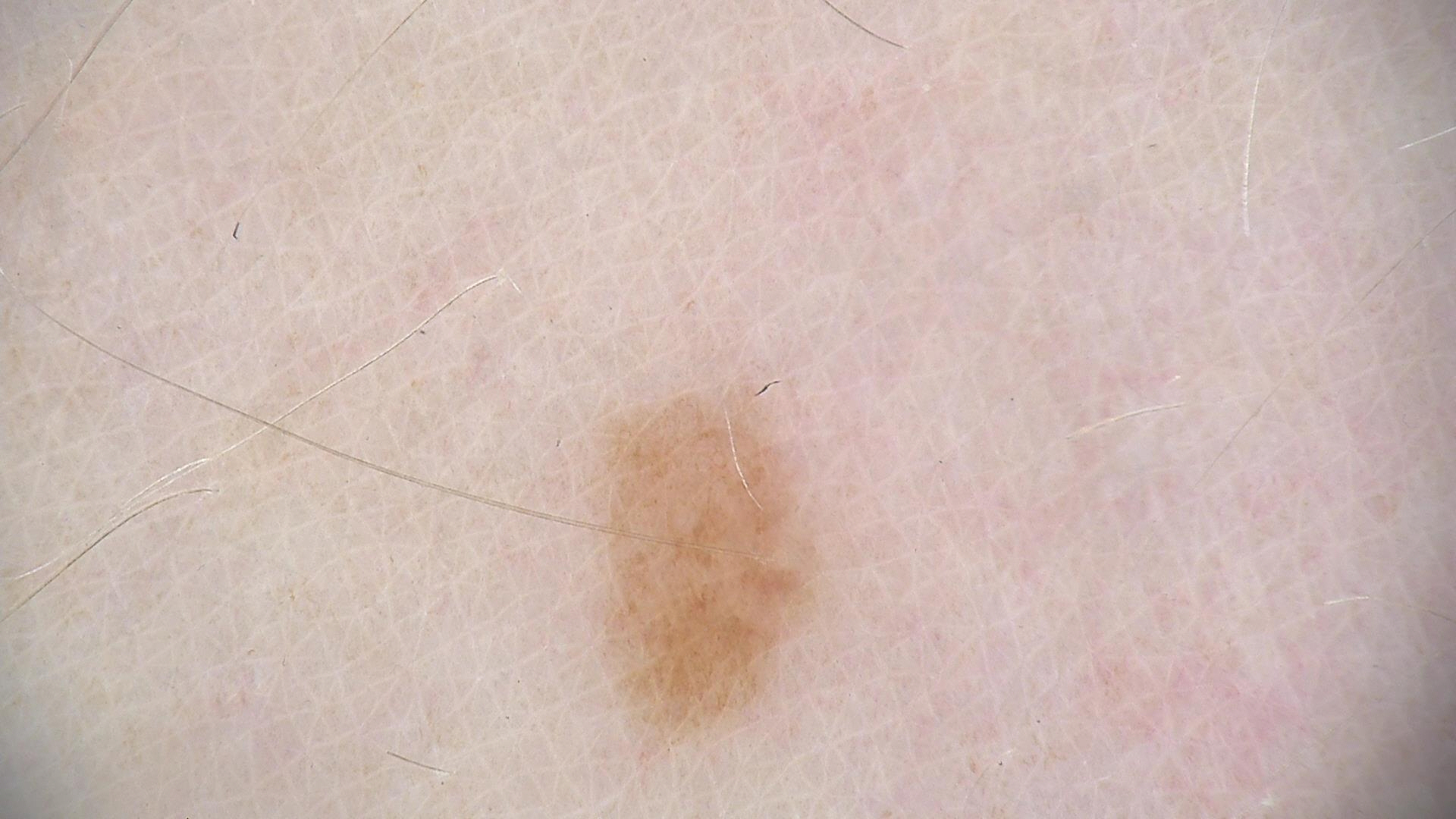Dermoscopy of a skin lesion.
The diagnostic label was a benign lesion — a dysplastic junctional nevus.